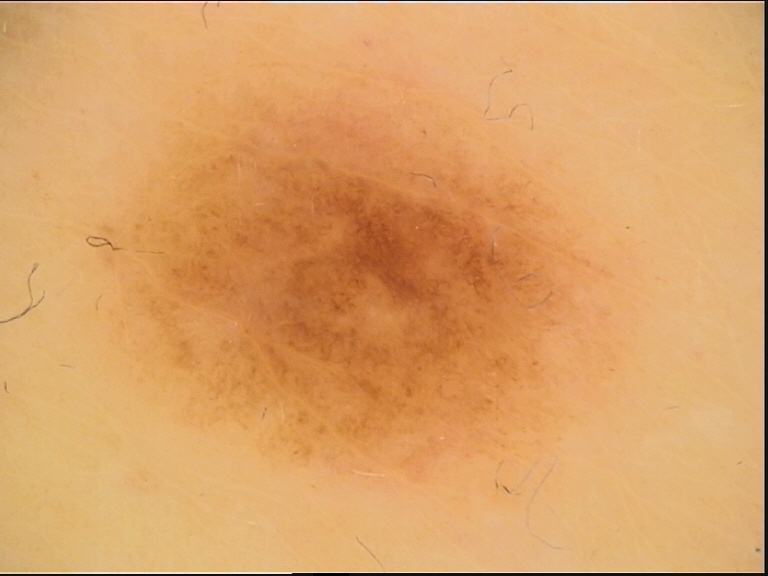Classified as a benign lesion — a dysplastic junctional nevus.